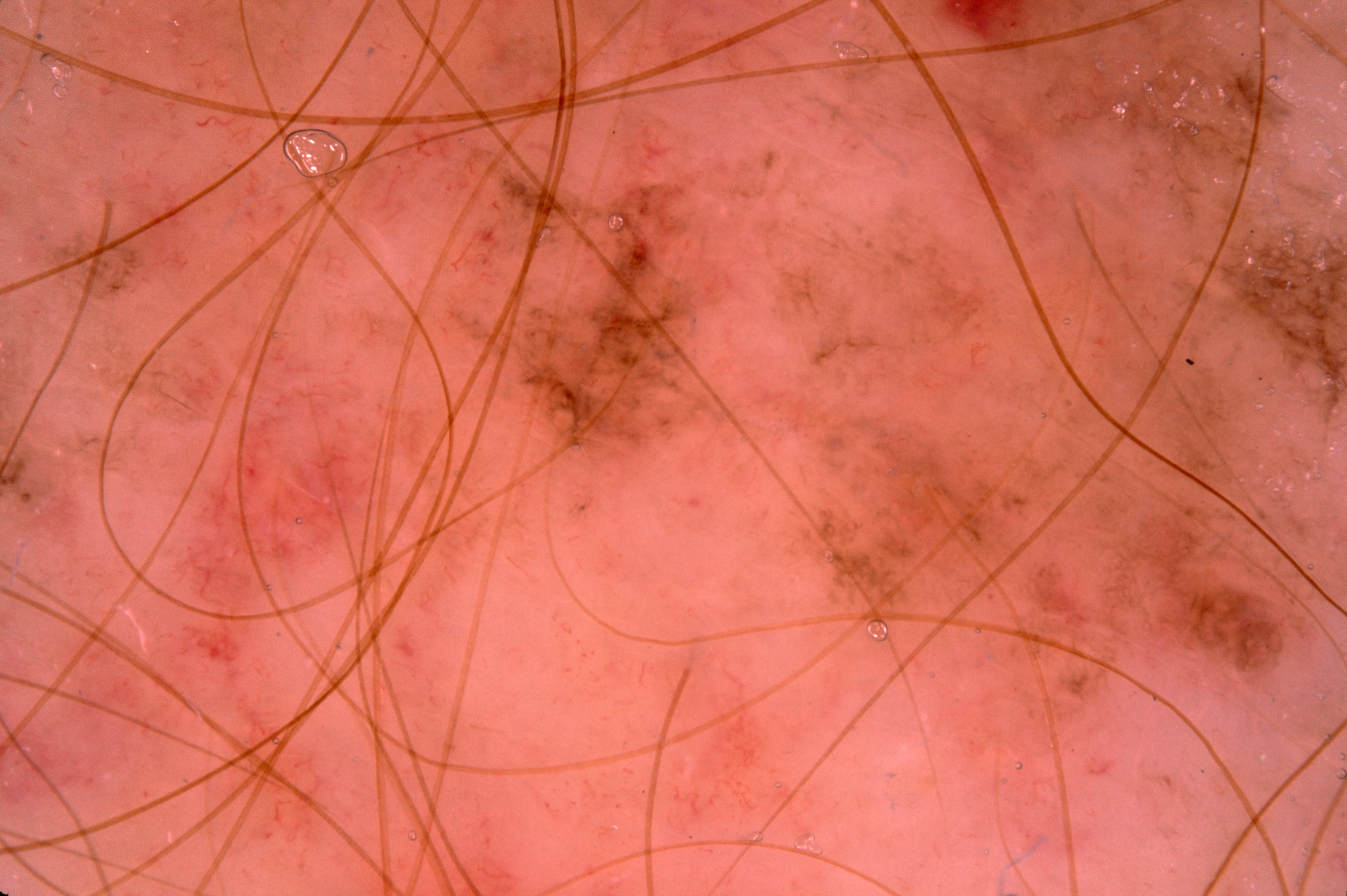A male patient approximately 70 years of age. A dermatoscopic image of a skin lesion. On dermoscopy, the lesion shows pigment network. The lesion occupies the region <box>421, 1, 1345, 866</box>. The lesion takes up a large portion of the image. Biopsy-confirmed as a melanoma.